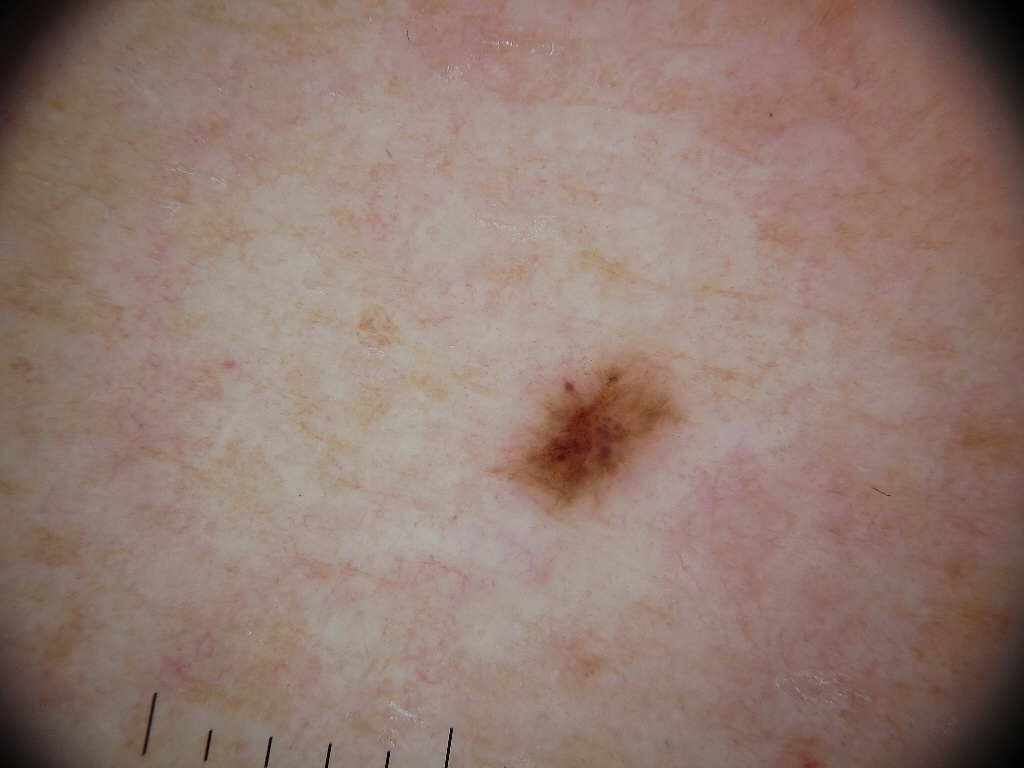A skin lesion imaged with a dermatoscope. Dermoscopic examination shows no milia-like cysts, streaks, pigment network, globules, or negative network. As (left, top, right, bottom), the lesion is located at 499, 352, 684, 517. Diagnosed as a melanocytic nevus.